Dermoscopy of a skin lesion: 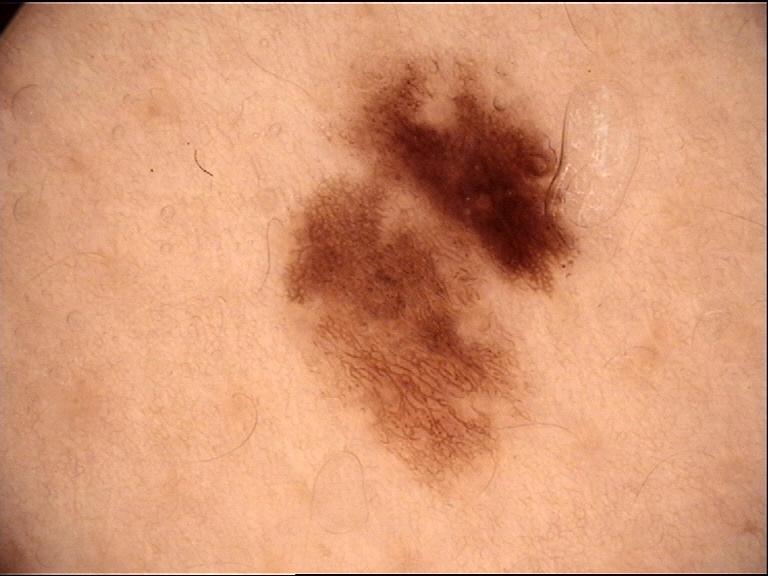– assessment · dysplastic junctional nevus (expert consensus)